A dermoscopic photograph of a skin lesion.
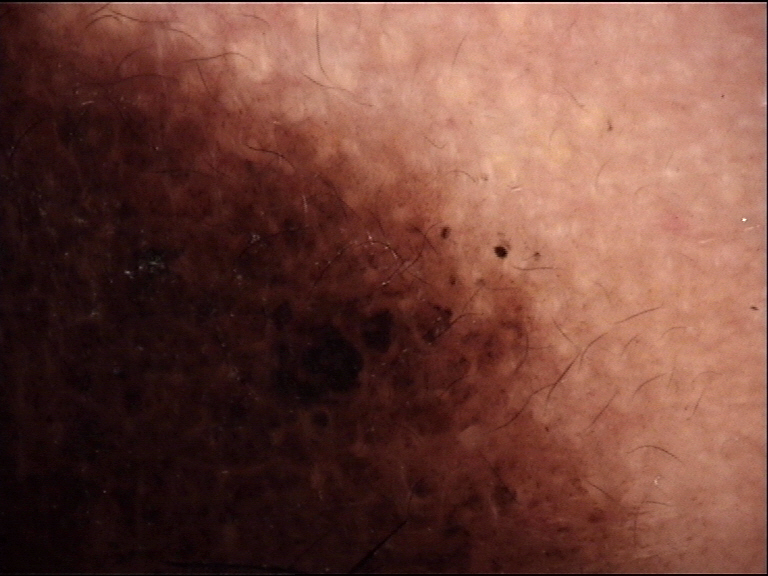Case:
This is a banal lesion.
Conclusion:
The diagnosis was a congenital compound nevus.